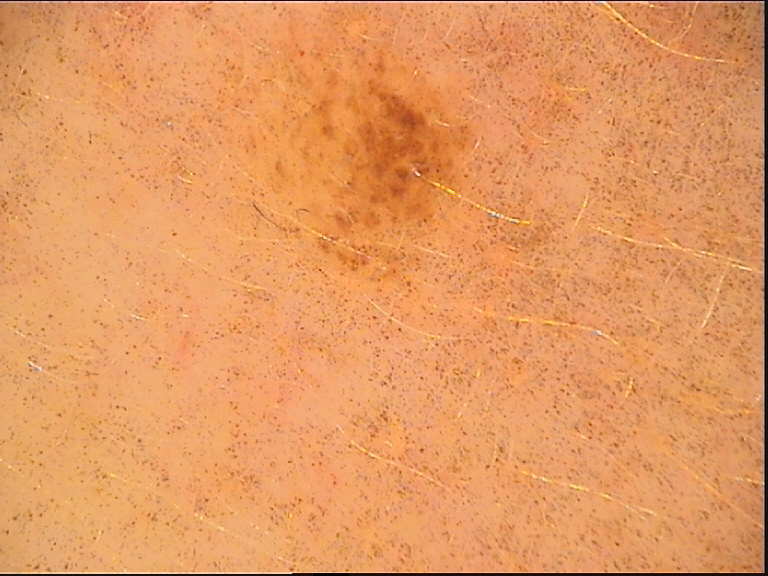{"diagnosis": {"name": "compound nevus", "code": "cb", "malignancy": "benign", "super_class": "melanocytic", "confirmation": "expert consensus"}}